Fitzpatrick phototype II; non-clinician graders estimated Monk skin tone scale 2 or 3, close-up view, the contributor notes the condition has been present for less than one week, the affected area is the head or neck, the lesion is associated with burning and itching:
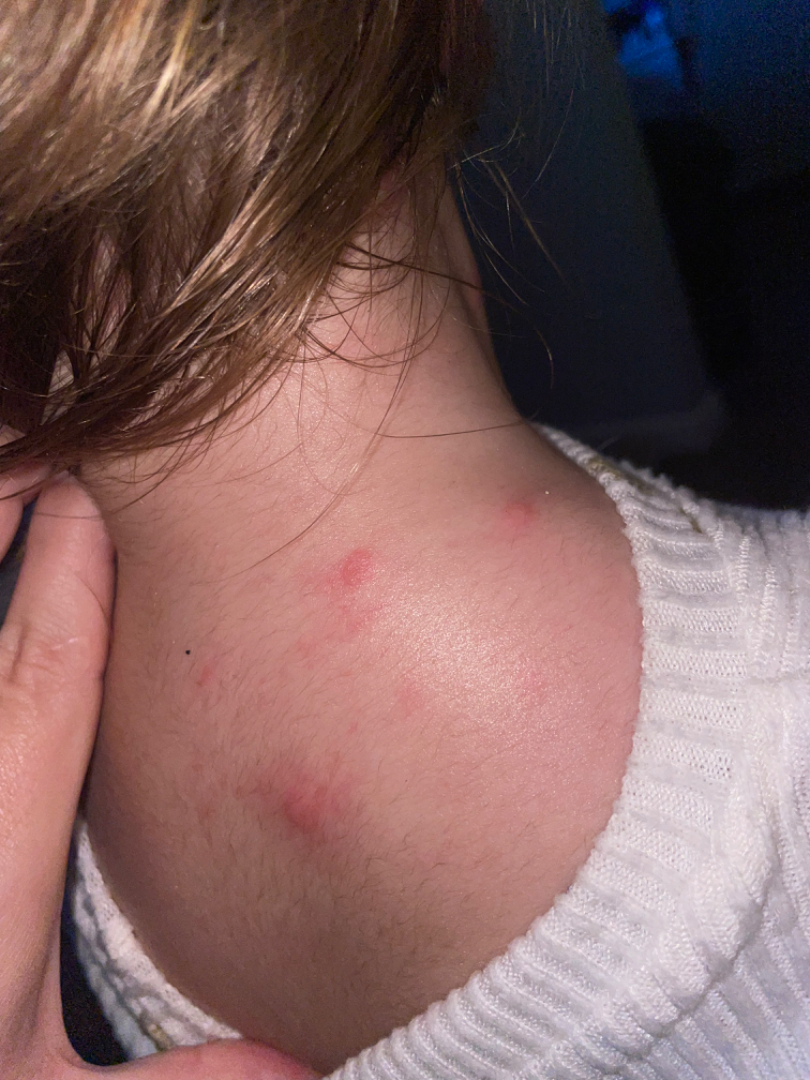* impression — Insect Bite and Acute dermatitis, NOS were considered with similar weight